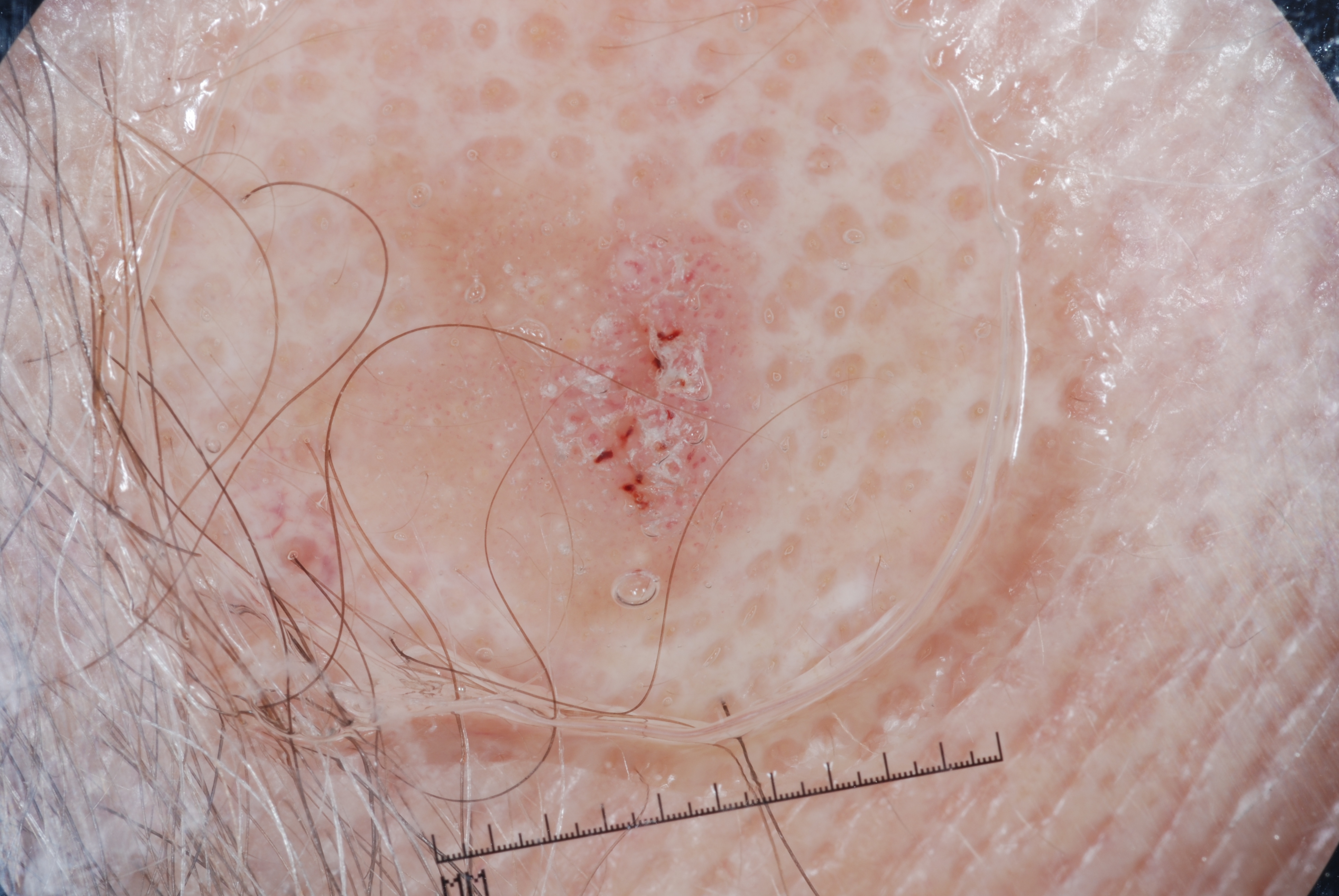Summary:
A skin lesion imaged with a dermatoscope. The subject is a male about 75 years old. Dermoscopic assessment notes milia-like cysts. The visible lesion spans bbox(181, 125, 771, 683). The lesion takes up a moderate portion of the field.
Impression:
Diagnosed as a seborrheic keratosis.